A dermoscopic close-up of a skin lesion:
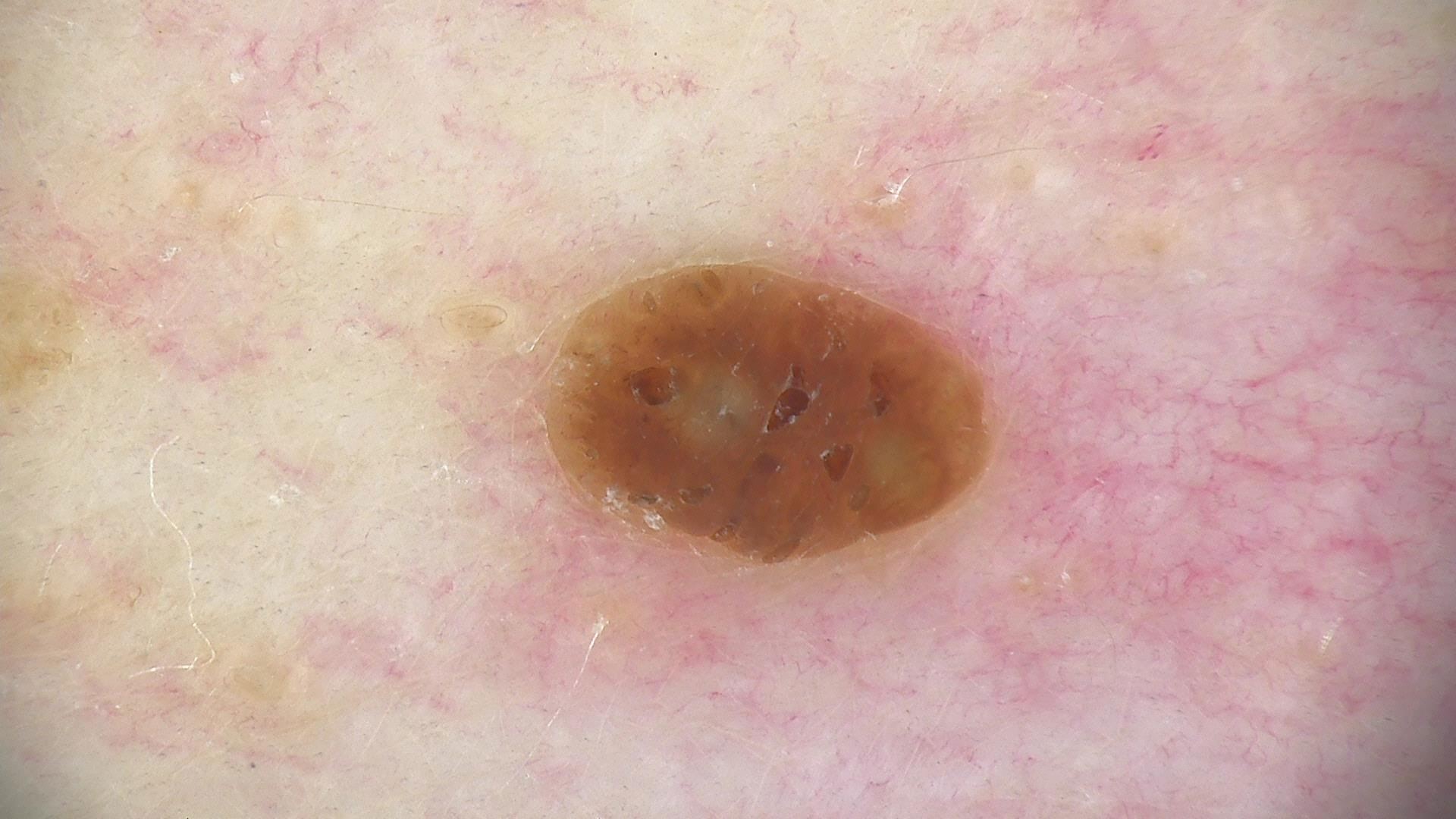{"diagnosis": {"name": "seborrheic keratosis", "code": "sk", "malignancy": "benign", "super_class": "non-melanocytic", "confirmation": "expert consensus"}}